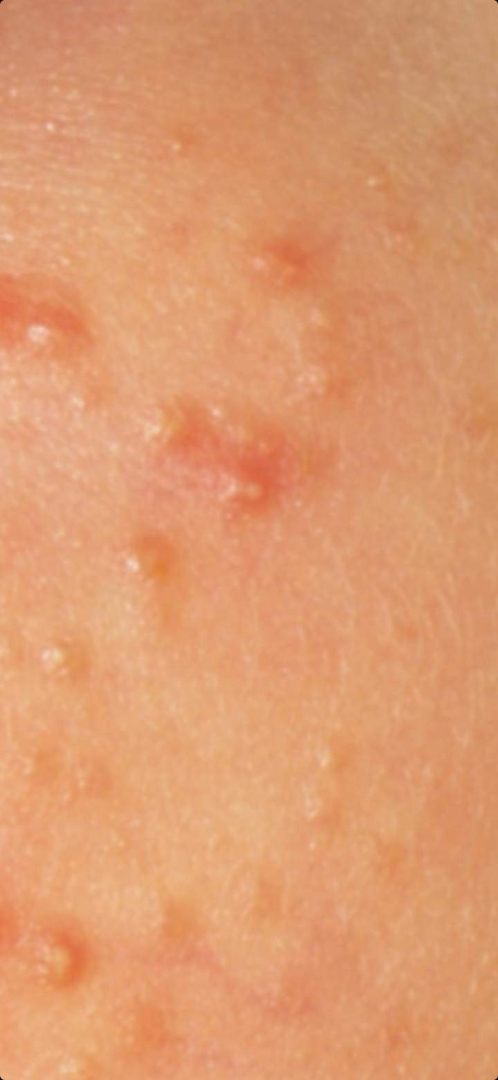History:
A close-up photograph. The patient is a male aged 18–29.
Impression:
On remote dermatologist review, the favored diagnosis is Acne.